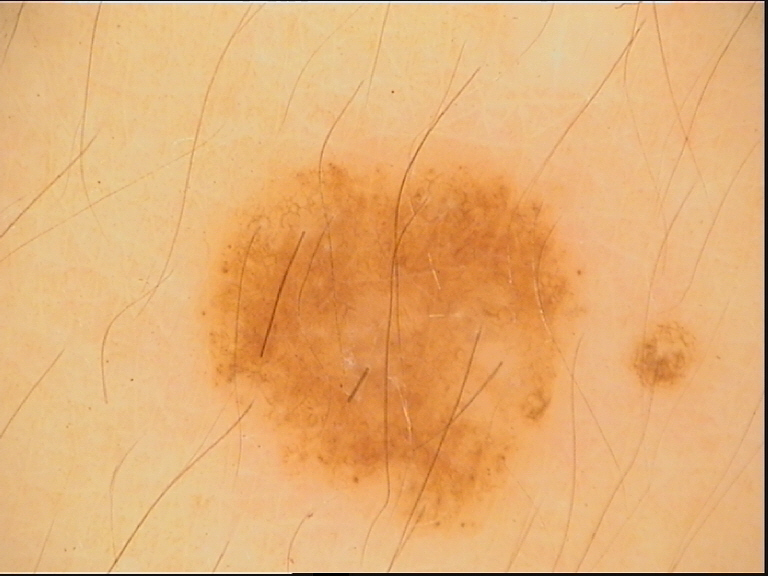Dermoscopy of a skin lesion.
The diagnosis was a dysplastic junctional nevus.